The arm is involved; the photograph is a close-up of the affected area: 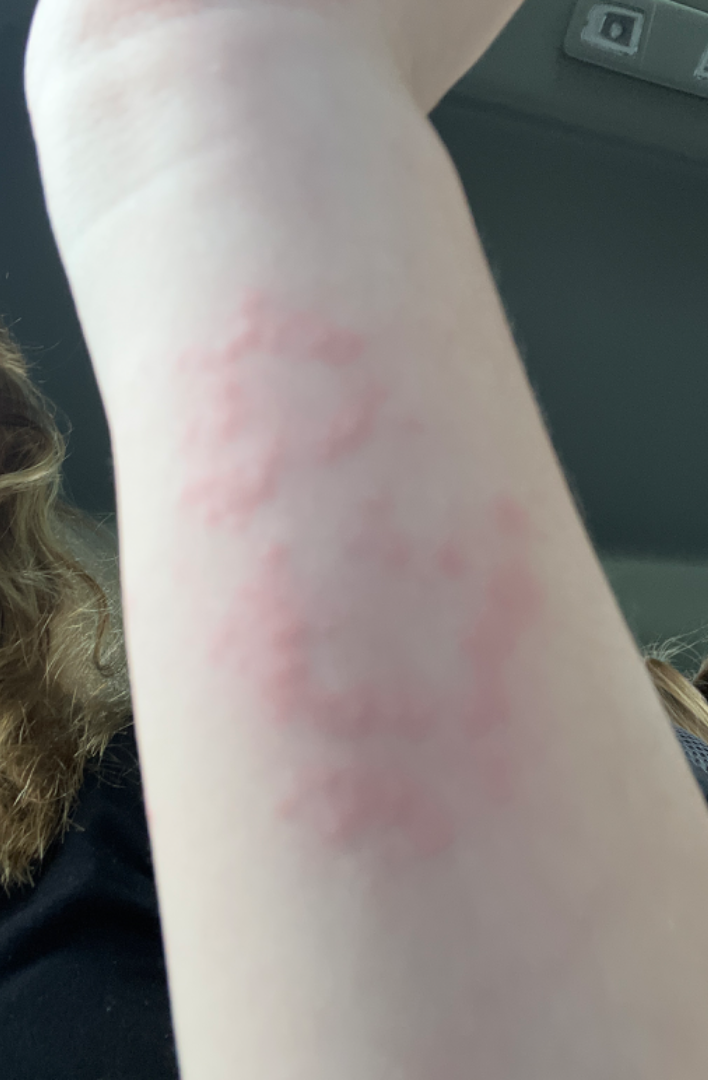Impression: The dermatologist could not determine a likely condition from the photograph alone.